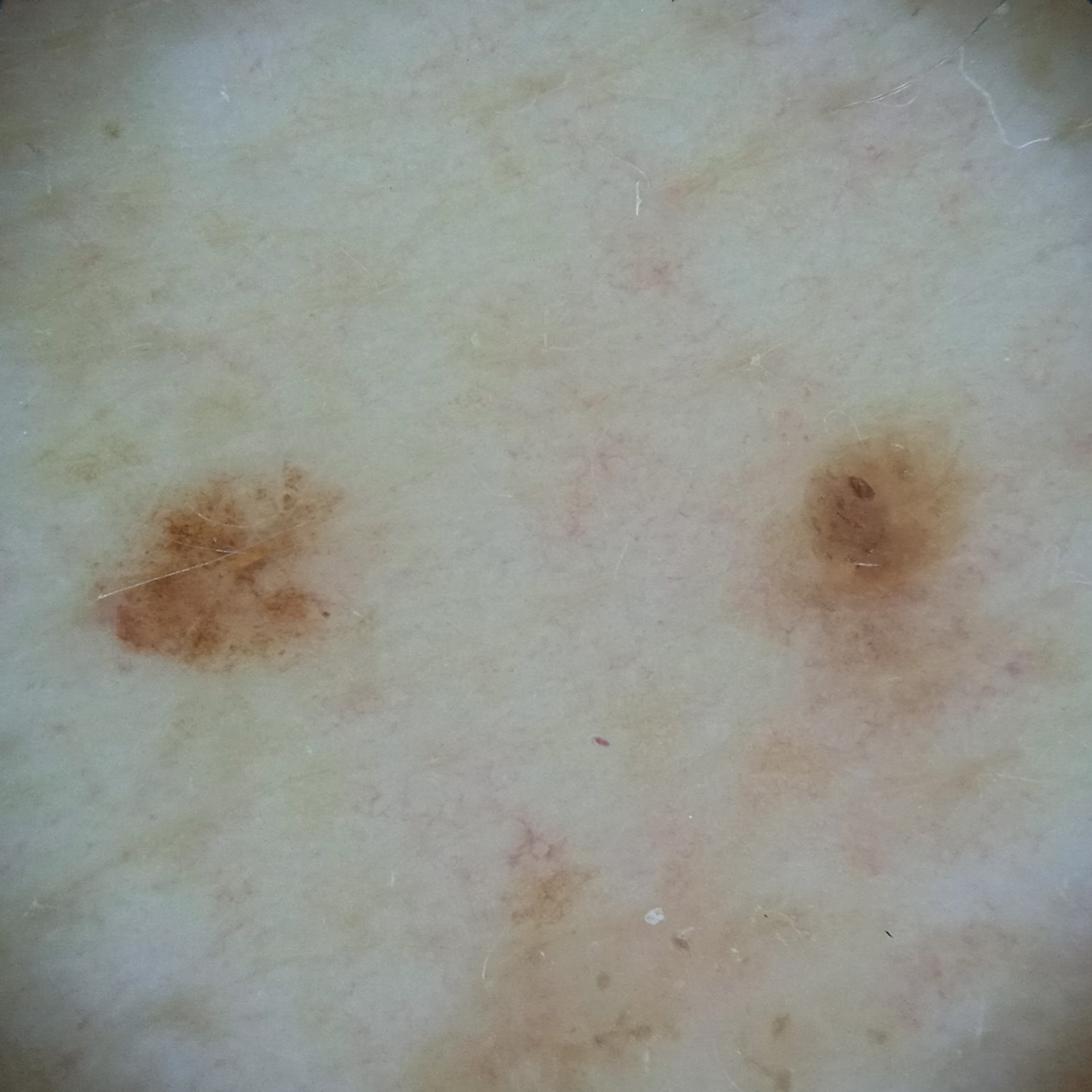patient=male, 78 years of age; image type=dermoscopic image; referral context=research study (no referral diagnosis); lesion size=3.1 mm; assessment=seborrheic keratosis (dermatologist consensus).